The patient was assessed as Fitzpatrick phototype II · a female patient in their mid-60s · a smartphone photograph of a skin lesion · history notes prior malignancy (patient or family) — 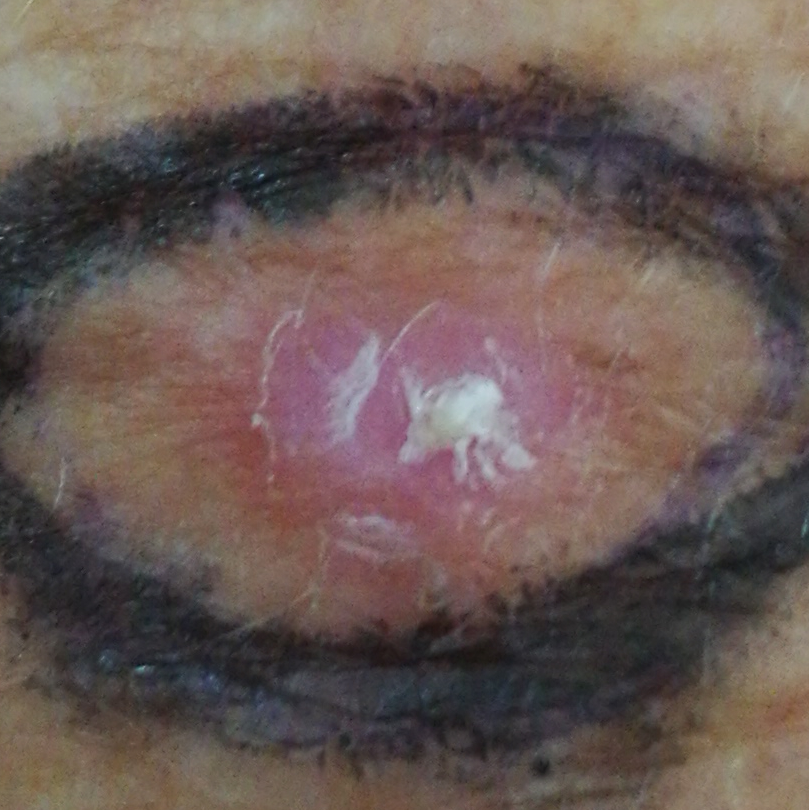<case>
<lesion_location>an arm</lesion_location>
<diagnosis>
<name>actinic keratosis</name>
<code>ACK</code>
<malignancy>indeterminate</malignancy>
<confirmation>histopathology</confirmation>
</diagnosis>
</case>